Female patient, age 40–49. The affected area is the head or neck. No associated systemic symptoms reported. The patient considered this a rash. The photograph is a close-up of the affected area. Reported lesion symptoms include pain, darkening, bothersome appearance and burning. The condition has been present for less than one week. Skin tone: self-reported Fitzpatrick skin type IV; human graders estimated Monk Skin Tone 2 or 3.
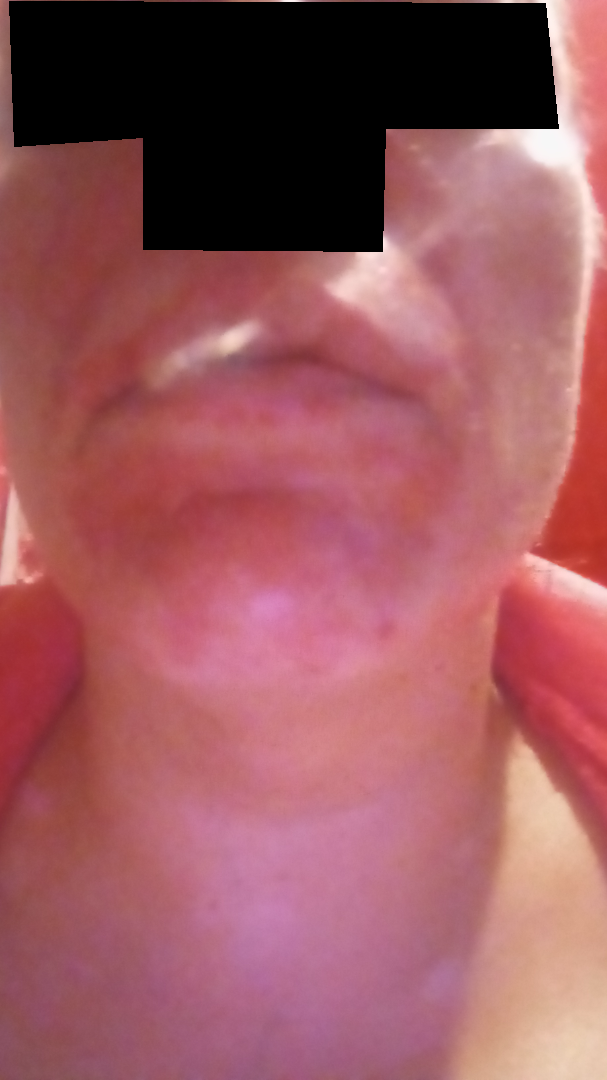Assessment: The dermatologist could not determine a likely condition from the photograph alone.